This is a close-up image. Symptoms reported: itching. Texture is reported as raised or bumpy:
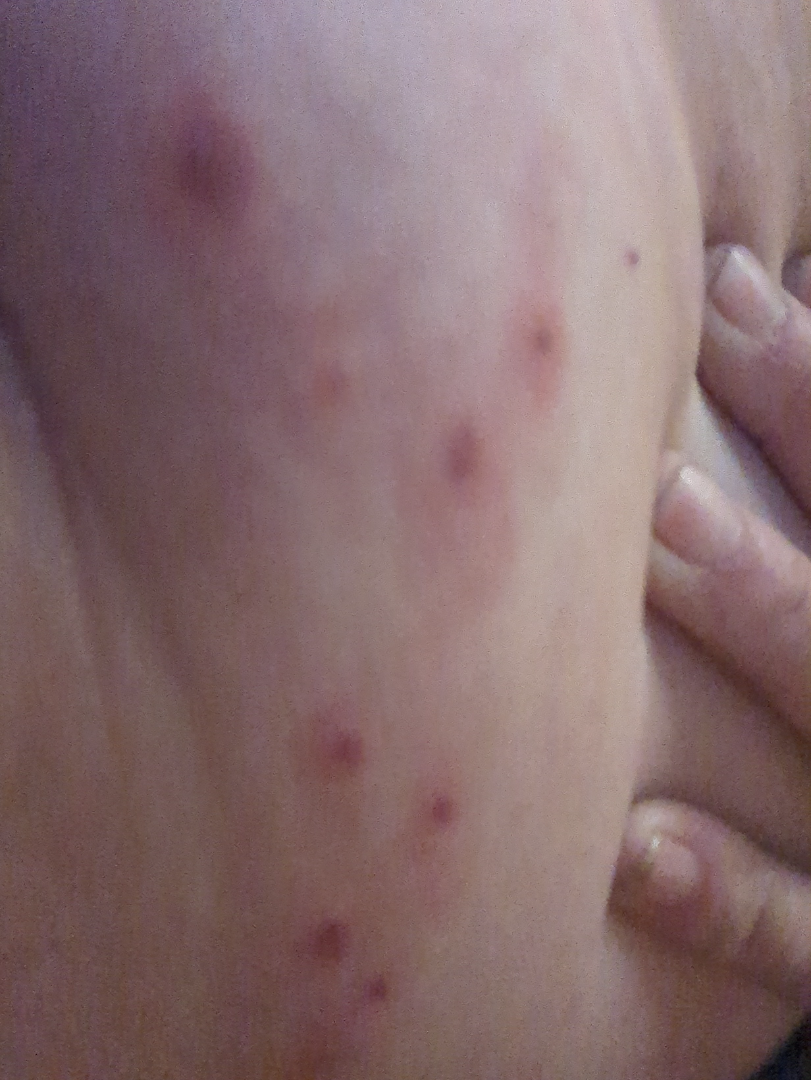On photographic review: consistent with Herpes Zoster.